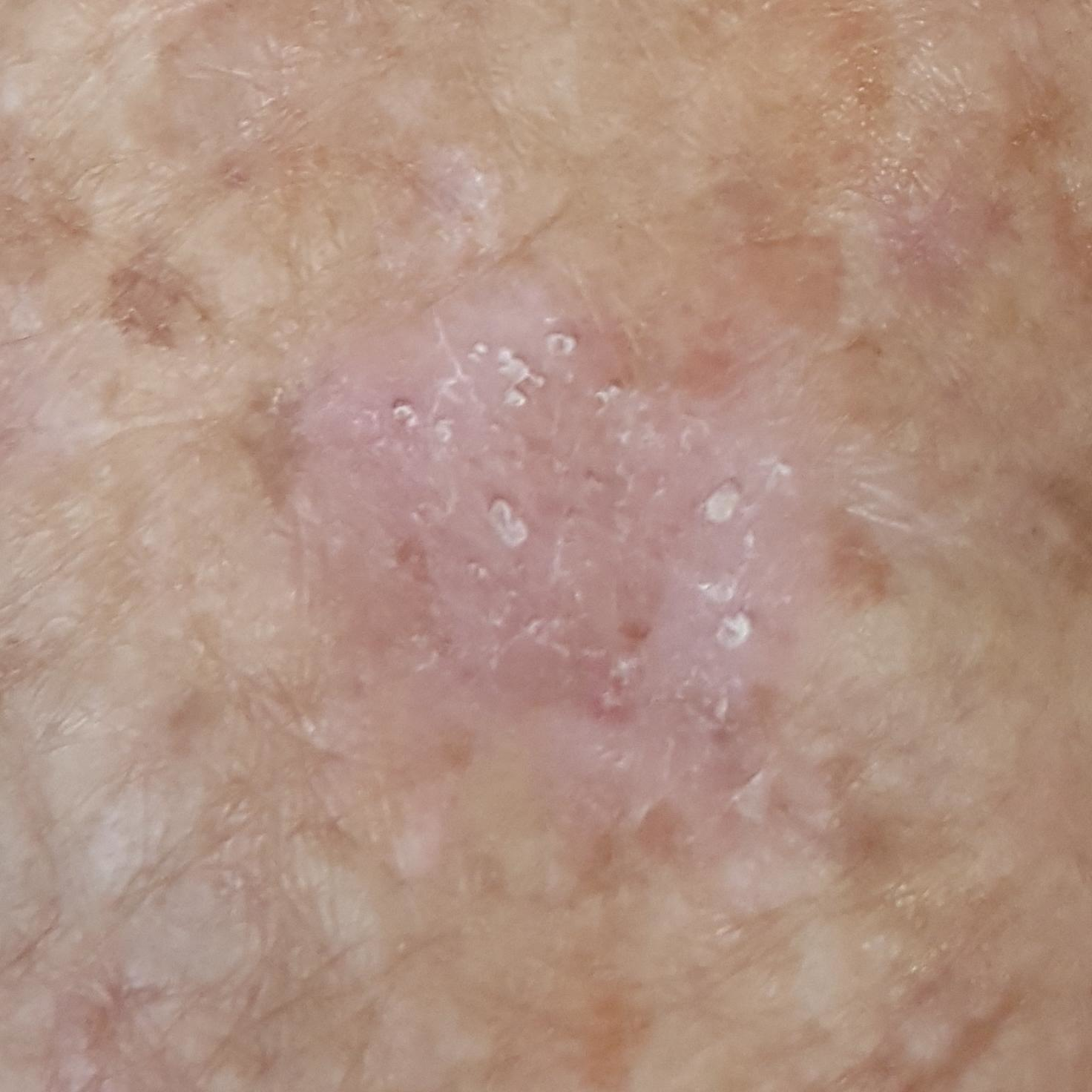Case:
– image · smartphone clinical photo
– patient · age 79
– region · an arm
– diagnostic label · actinic keratosis (clinical consensus)